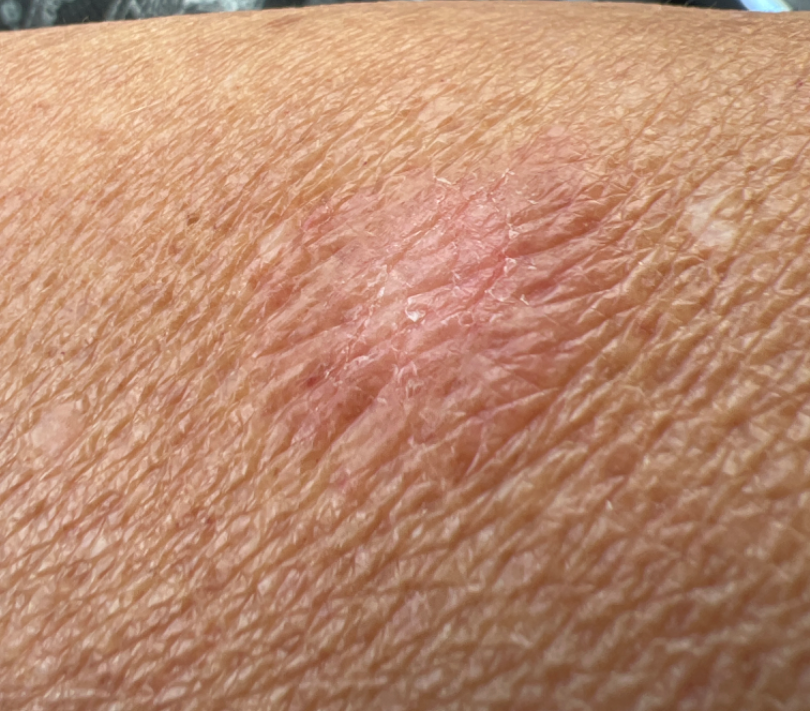assessment = indeterminate.